A skin lesion imaged with a dermatoscope · a female patient, aged 43-47 — 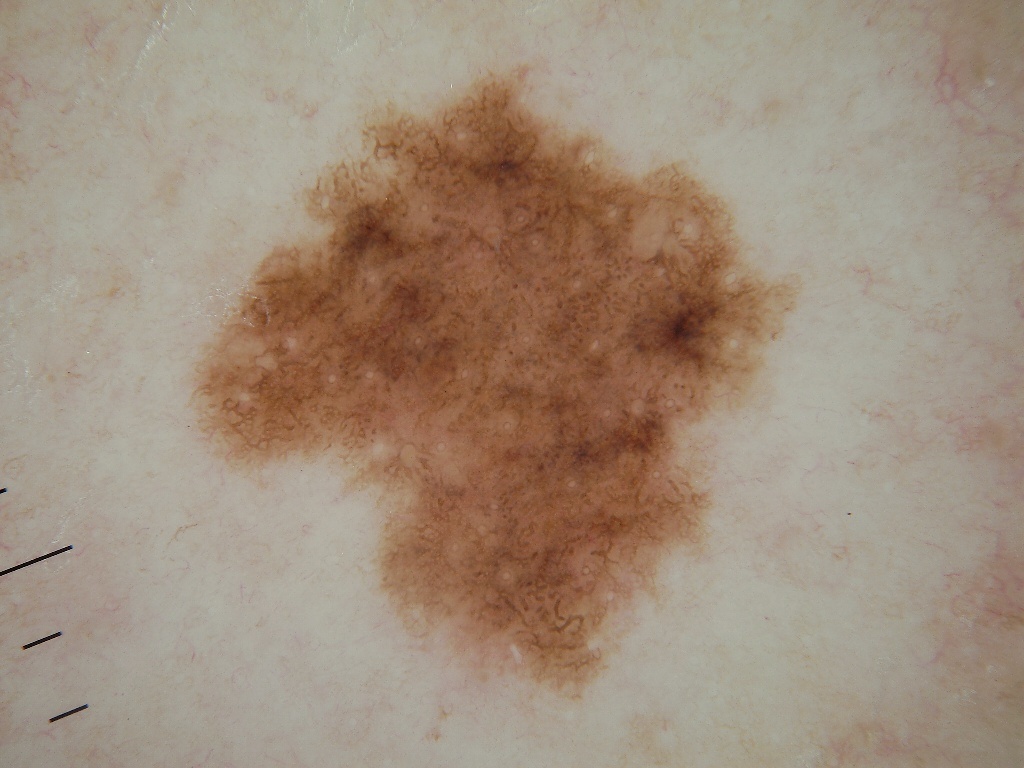Findings:
Dermoscopic assessment notes pigment network; no streaks, negative network, globules, or milia-like cysts. The lesion is bounded by bbox=[193, 63, 797, 698]. A moderately sized lesion.
Conclusion:
Clinically diagnosed as a melanocytic nevus, a benign skin lesion.